Acquired for a research image collection, with no referral diagnosis. A male patient age 72. A clinical photograph of a skin lesion.
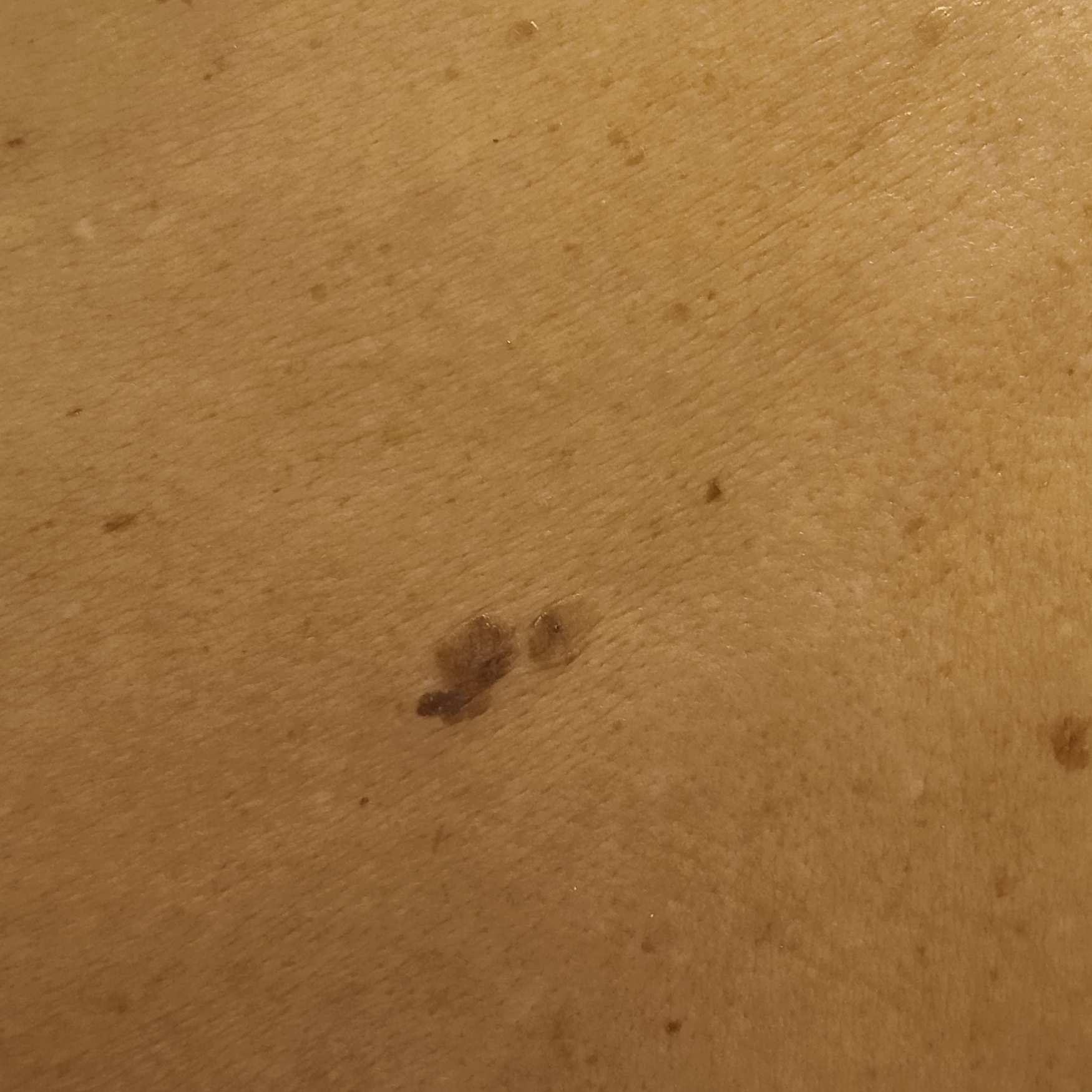Clinical context:
Located on the back. The lesion measures approximately 12.8 mm.
Conclusion:
The diagnostic impression was a seborrheic keratosis.